Recorded as Fitzpatrick skin type II · contact-polarized dermoscopy of a skin lesion · a female subject approximately 65 years of age — 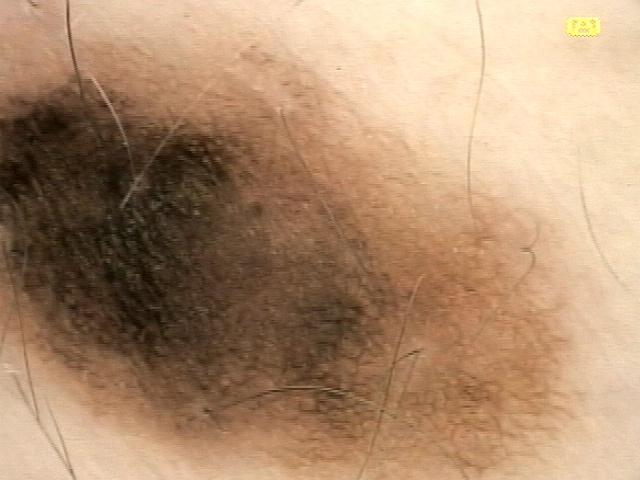body site=the trunk | diagnostic label=Nevus (biopsy-proven).